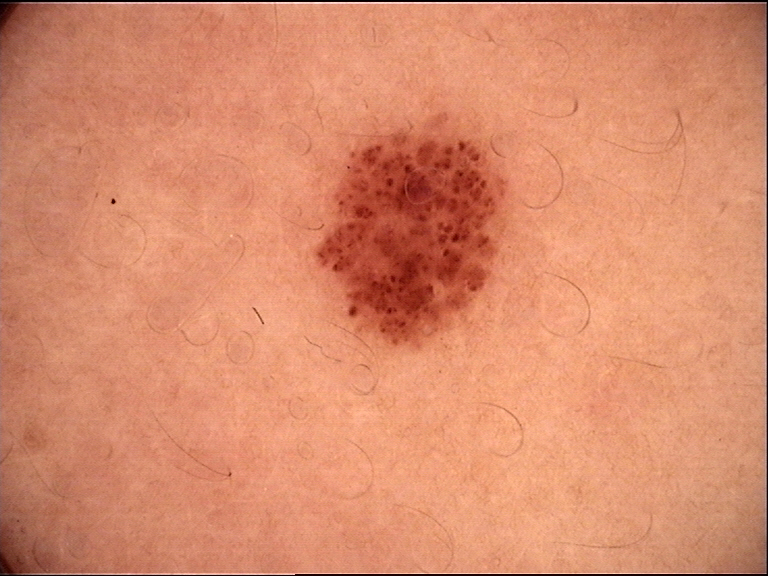A dermoscopic close-up of a skin lesion. The morphology is that of a banal lesion. Classified as a junctional nevus.